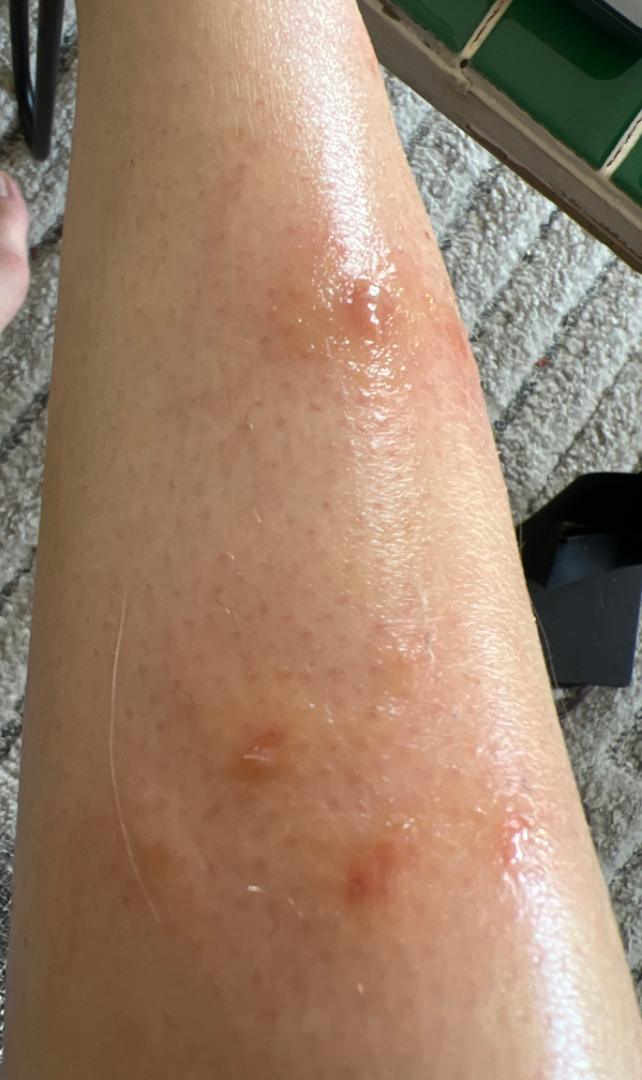Q: Patient's own categorization?
A: a rash
Q: What is the framing?
A: close-up
Q: Where on the body?
A: leg and top or side of the foot
Q: Texture?
A: fluid-filled
Q: Reported symptoms?
A: burning and itching
Q: What conditions are considered?
A: consistent with Eczema